A subject age 73 · a clinical photograph showing a skin lesion:
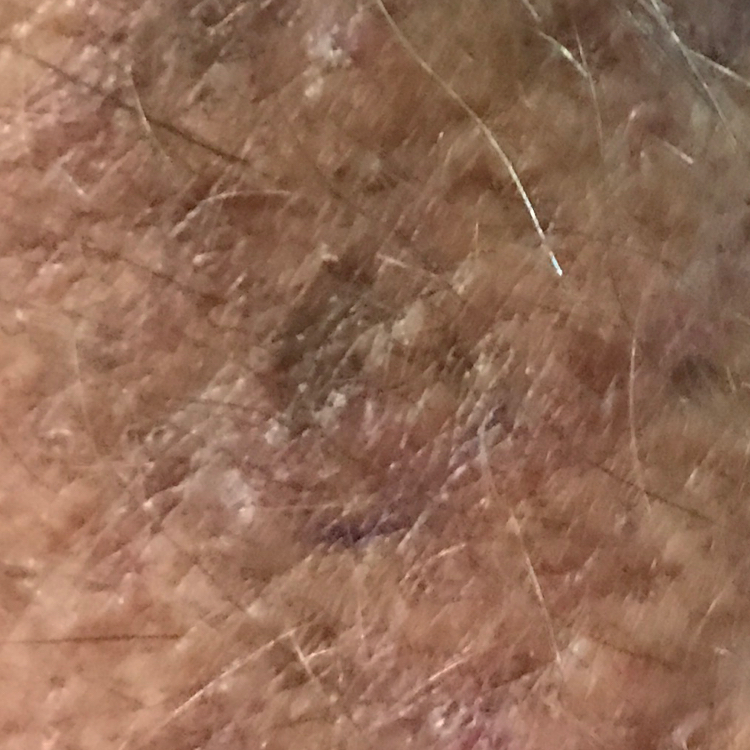– location: a forearm
– diagnostic label: actinic keratosis (clinical consensus)